A dermatoscopic image of a skin lesion:
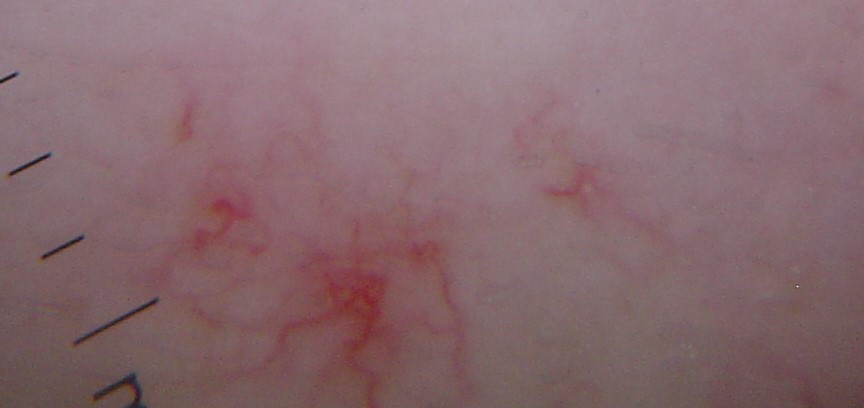Q: What is the diagnosis?
A: spider angioma (expert consensus)